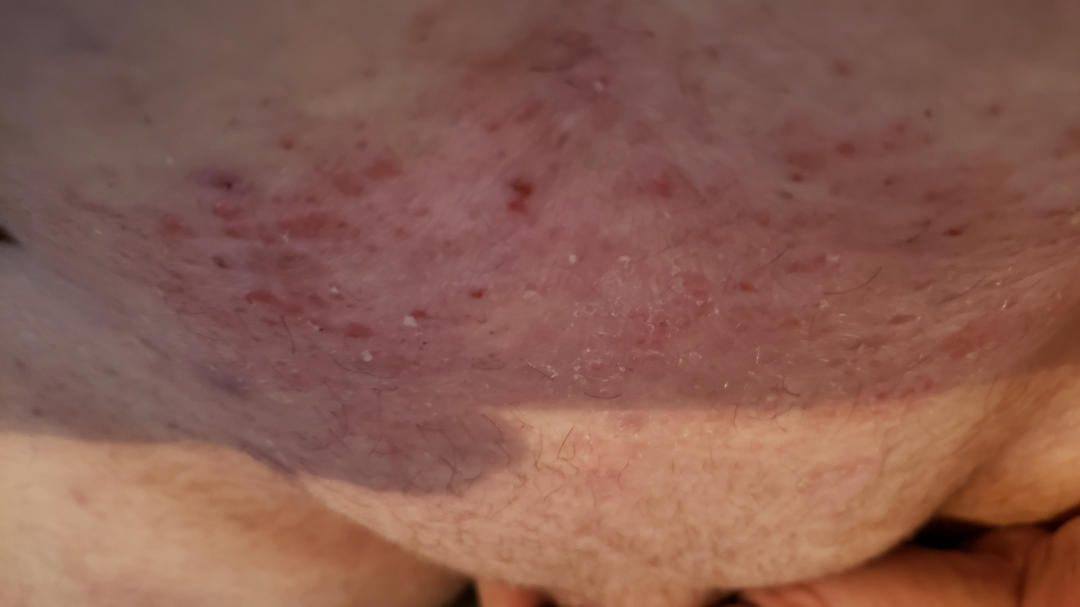Q: Patient demographics?
A: male, age 40–49
Q: Image view?
A: at an angle
Q: Where on the body?
A: front of the torso
Q: What is the dermatologist's impression?
A: Lichenified eczematous dermatitis (100%)